A dermoscopic image of a skin lesion.
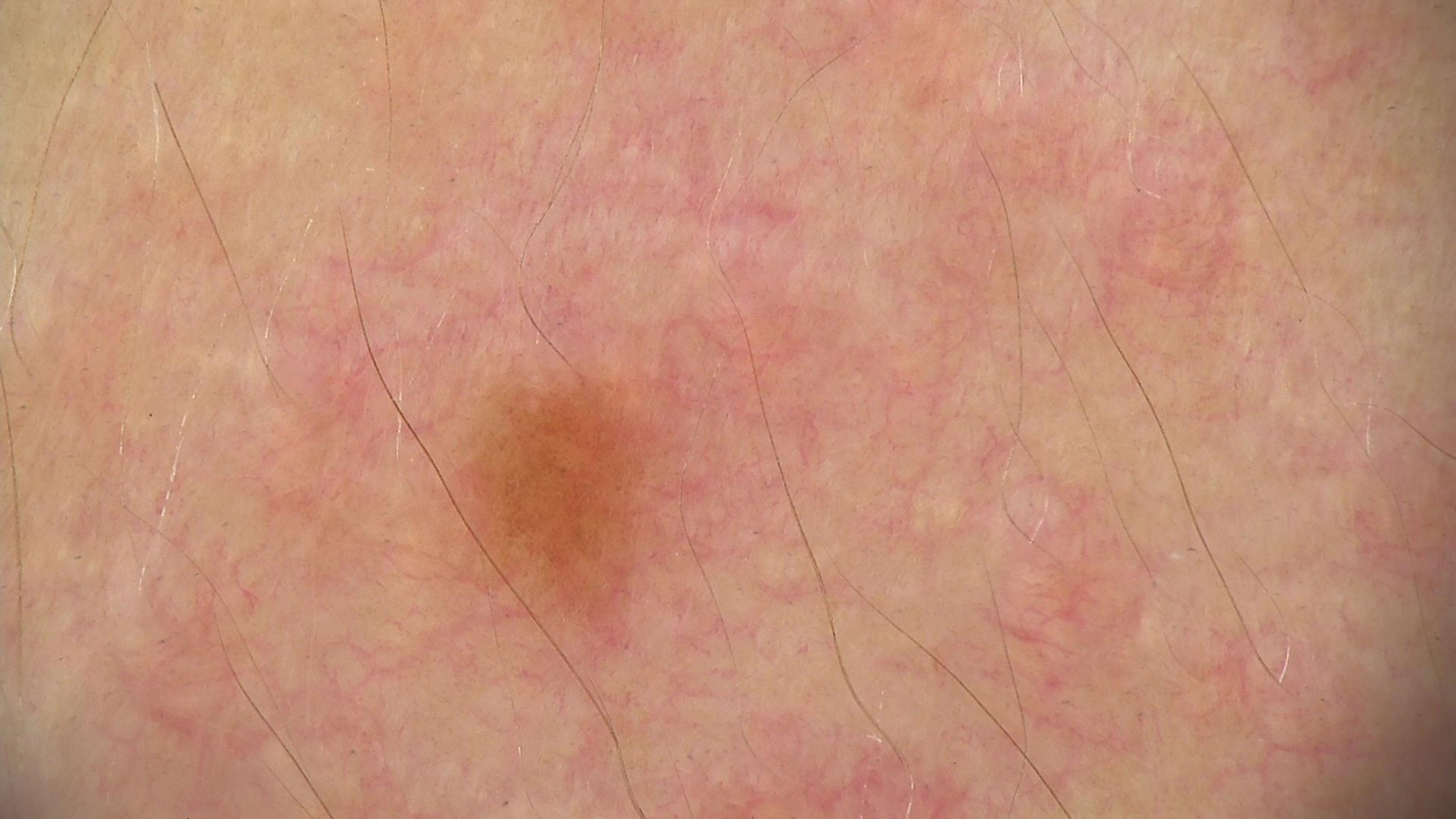diagnosis:
  name: dysplastic junctional nevus
  code: jd
  malignancy: benign
  super_class: melanocytic
  confirmation: expert consensus